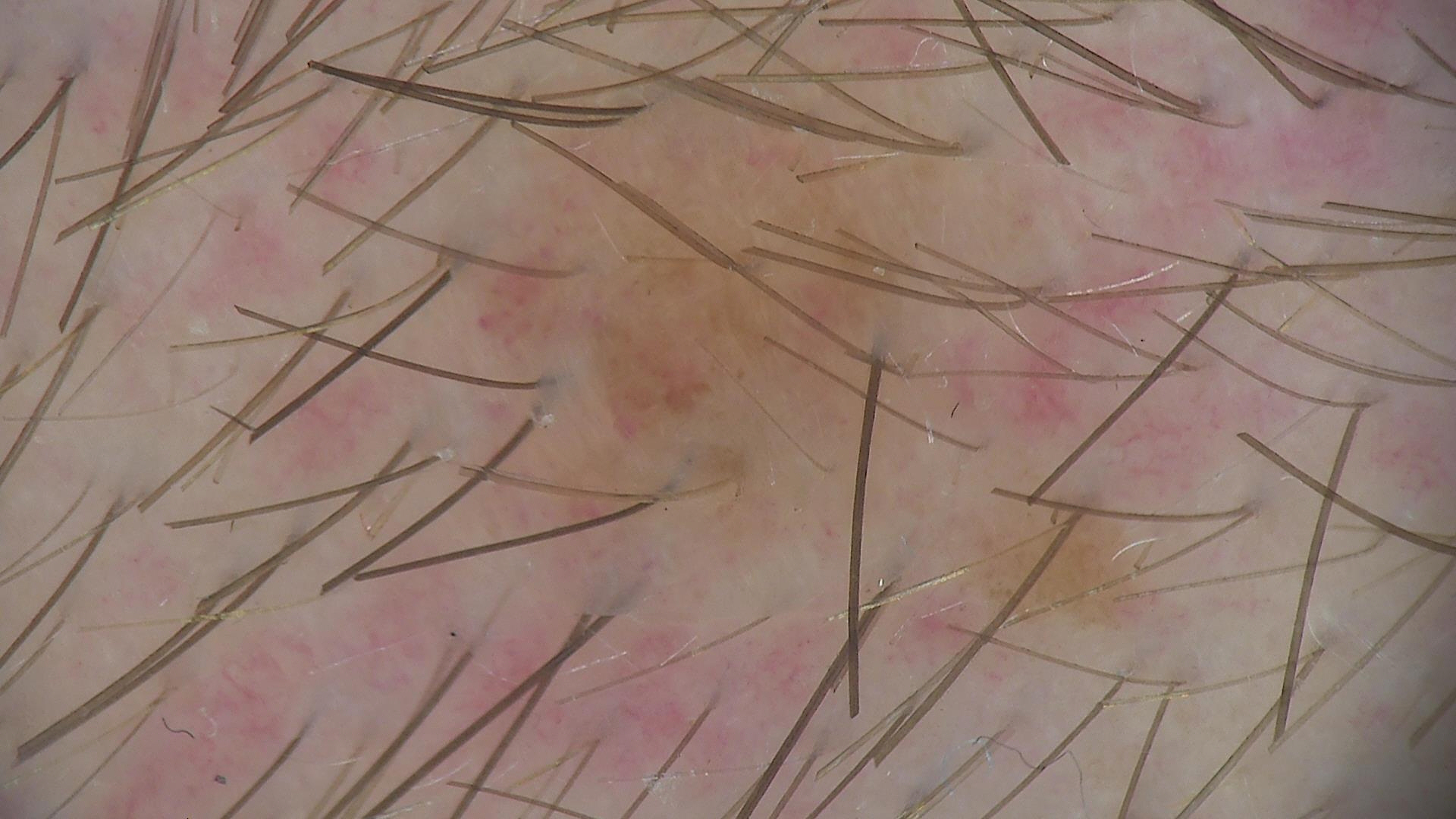diagnosis=dysplastic junctional nevus (expert consensus).